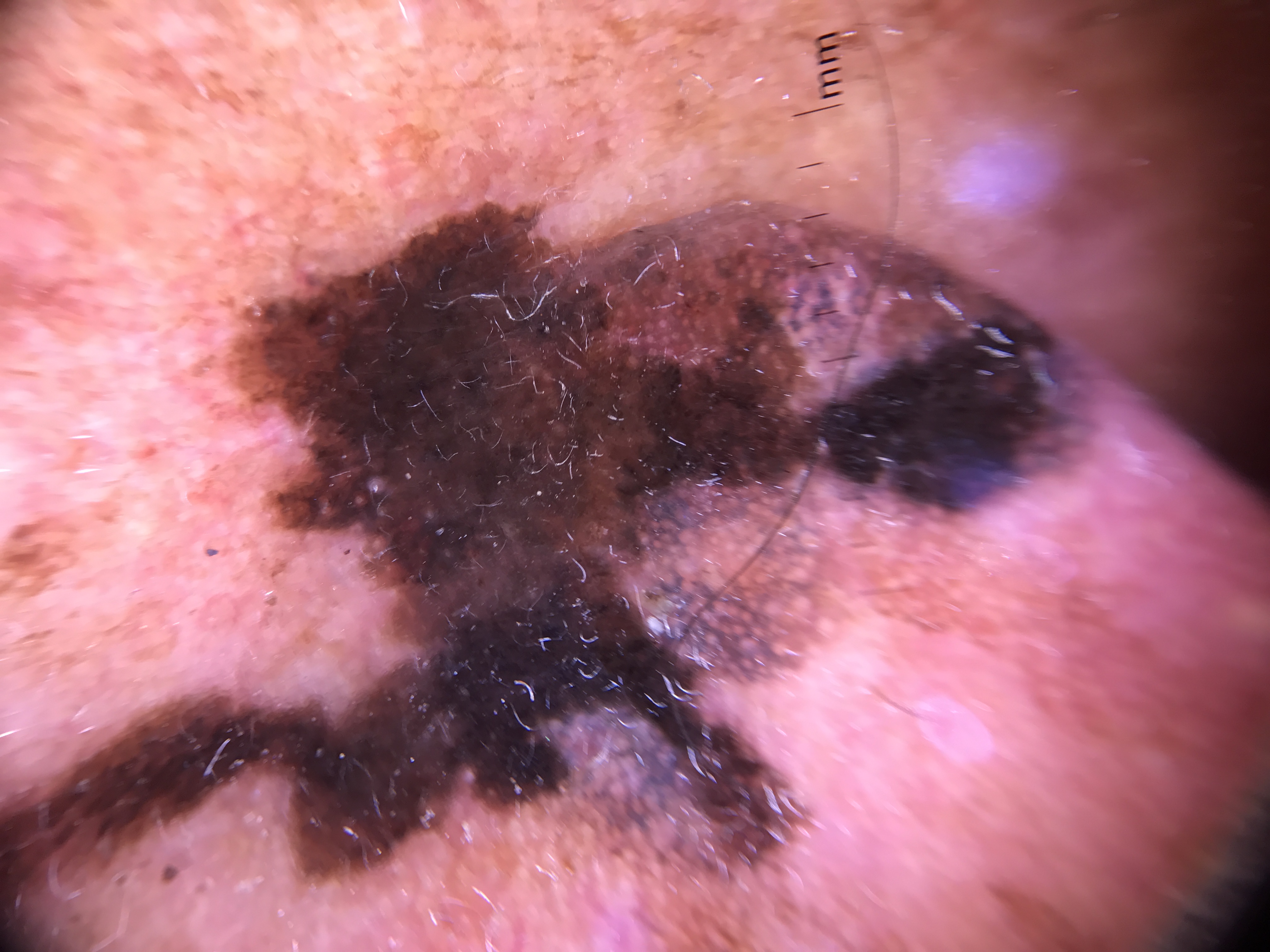Histopathology confirmed a lentigo maligna.